Present for less than one week. The contributor is female. Close-up view. The arm is involved. Self-categorized by the patient as a rash. The contributor reports the lesion is raised or bumpy.
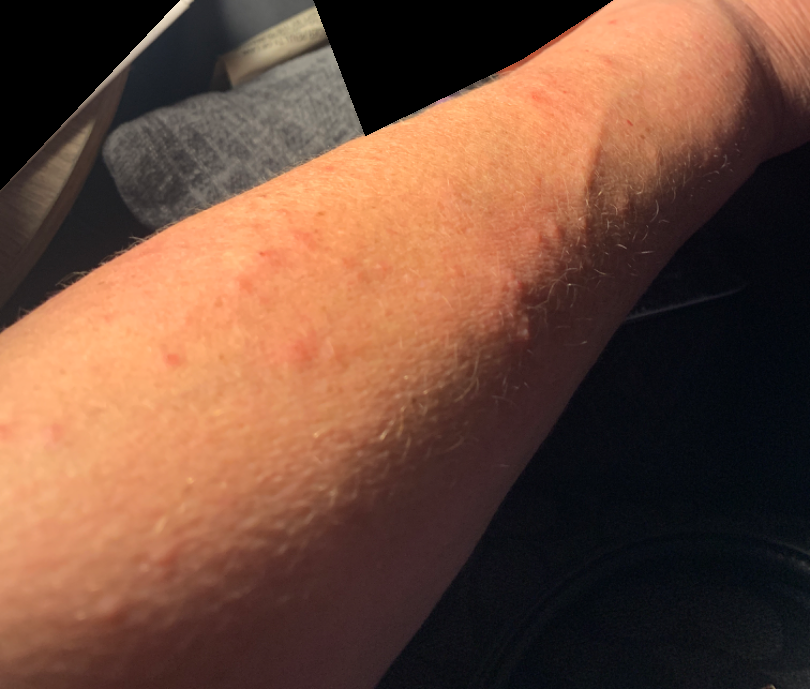On dermatologist assessment of the image: the differential includes Contact dermatitis and Allergic Contact Dermatitis, with no clear leading consideration; also raised was Folliculitis.